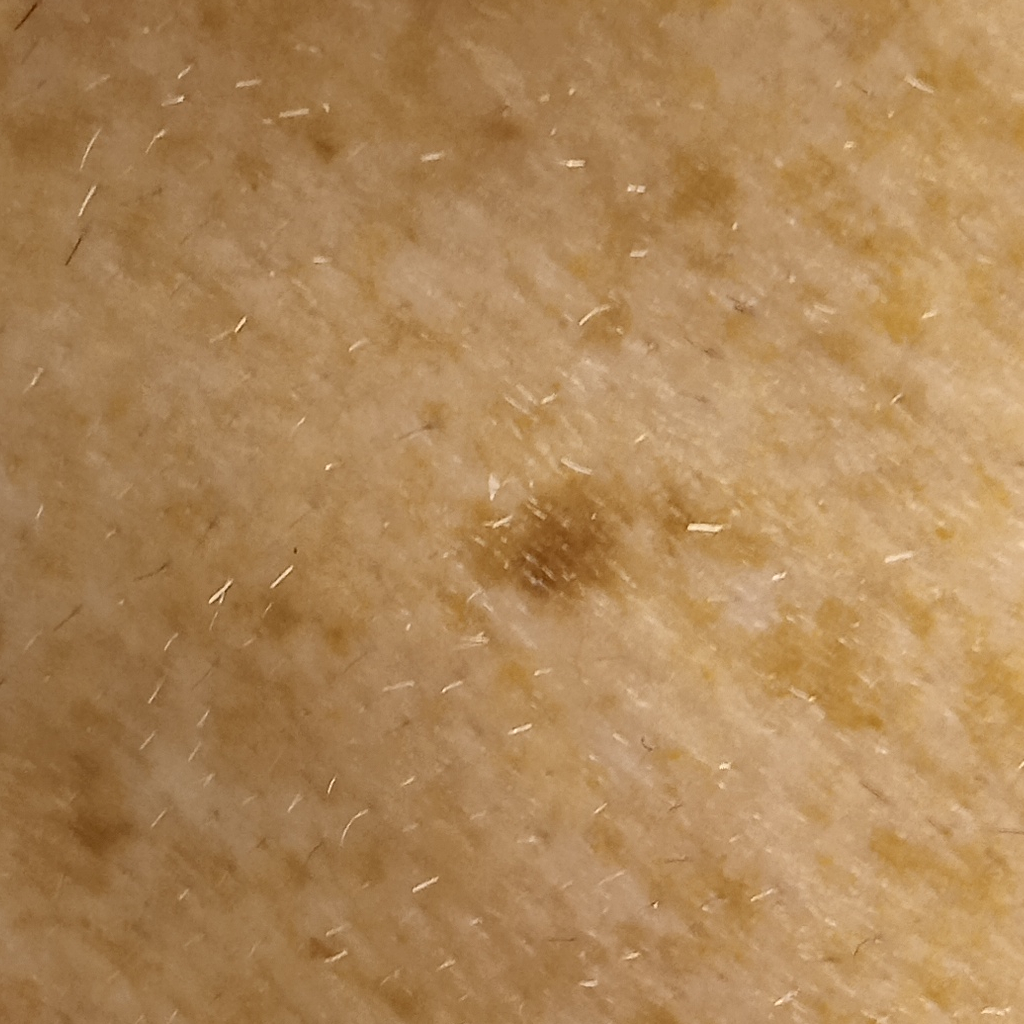- diagnostic label · melanoma (dermatologist consensus)